Close-up view · texture is reported as raised or bumpy.
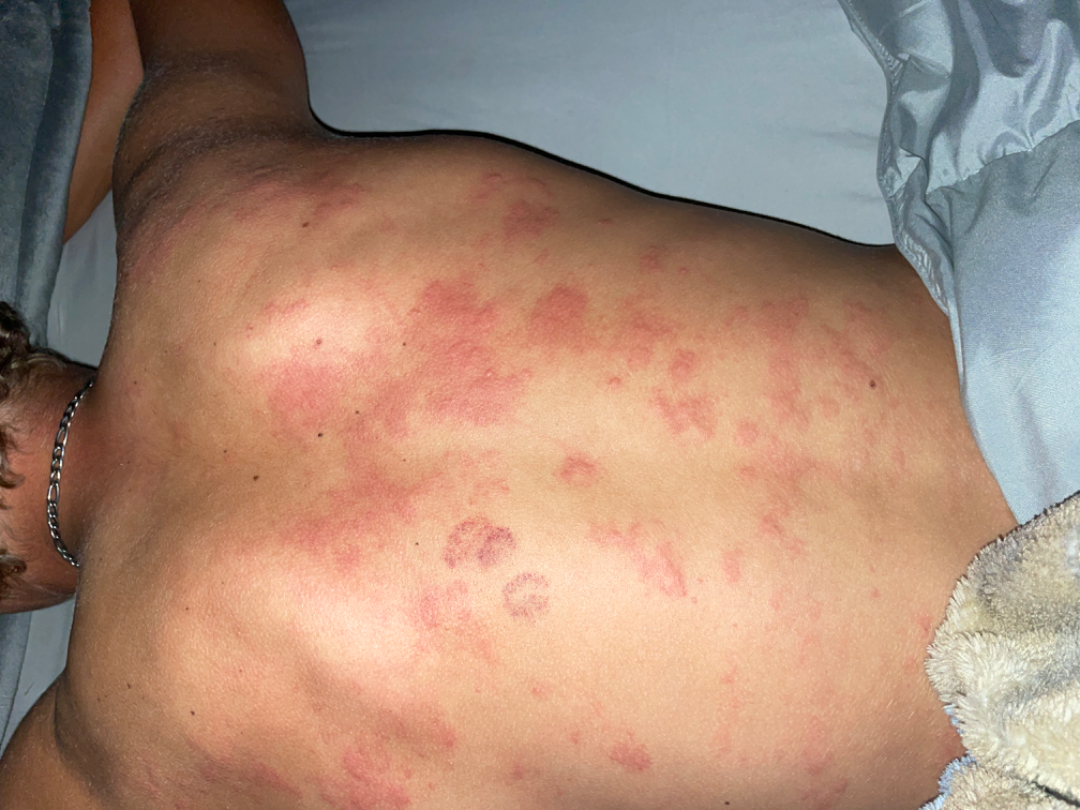On photographic review by a dermatologist, the reviewer's impression was Acute dermatitis, NOS.